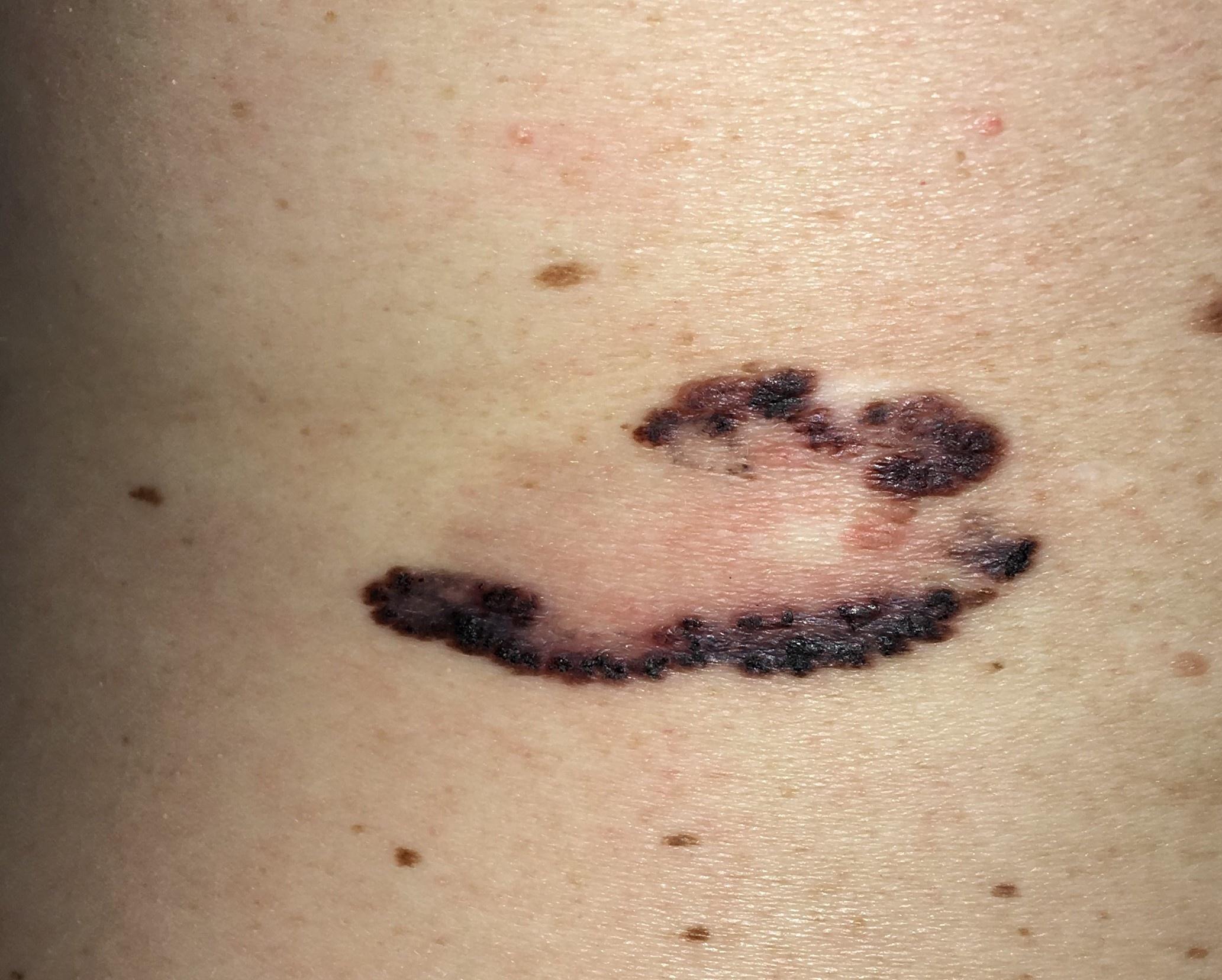A clinical photograph of a skin lesion.
A female patient in their mid-70s.
The lesion involves the trunk.
Histopathology confirmed a melanoma.